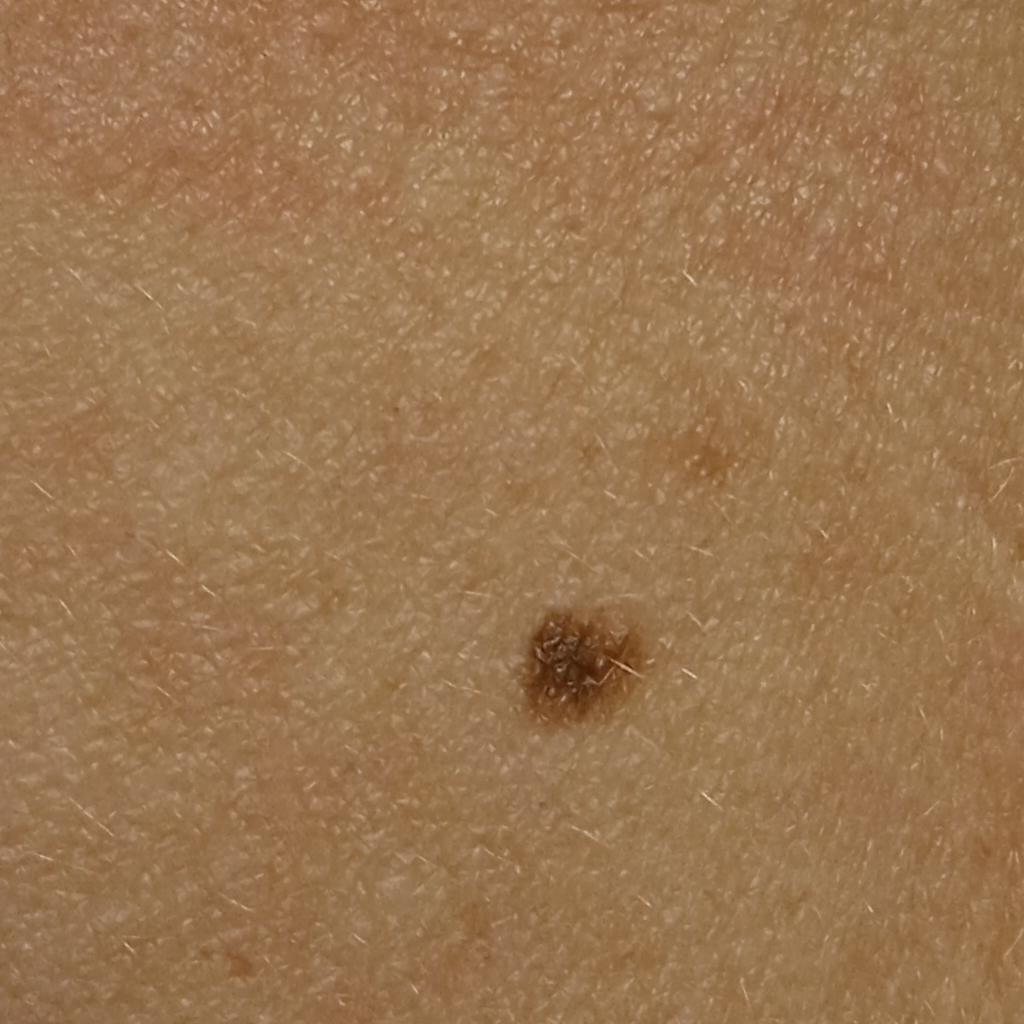Findings:
Imaged for a research study, with no referral diagnosis recorded. A female patient age 50. The lesion is on the torso. The lesion measures approximately 5.4 mm.
Impression:
The dermatologists' assessment was a melanocytic nevus.